Located on the arm; close-up view — 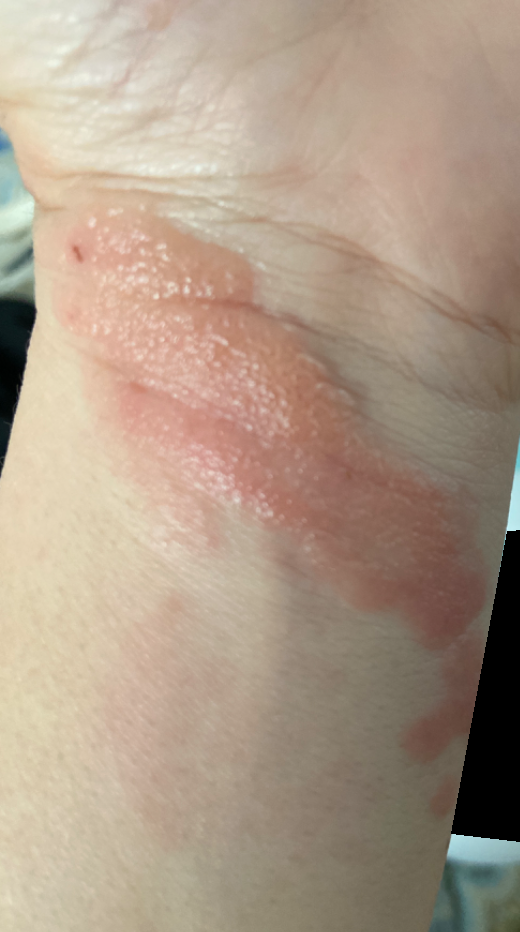{"differential": "Allergic Contact Dermatitis"}